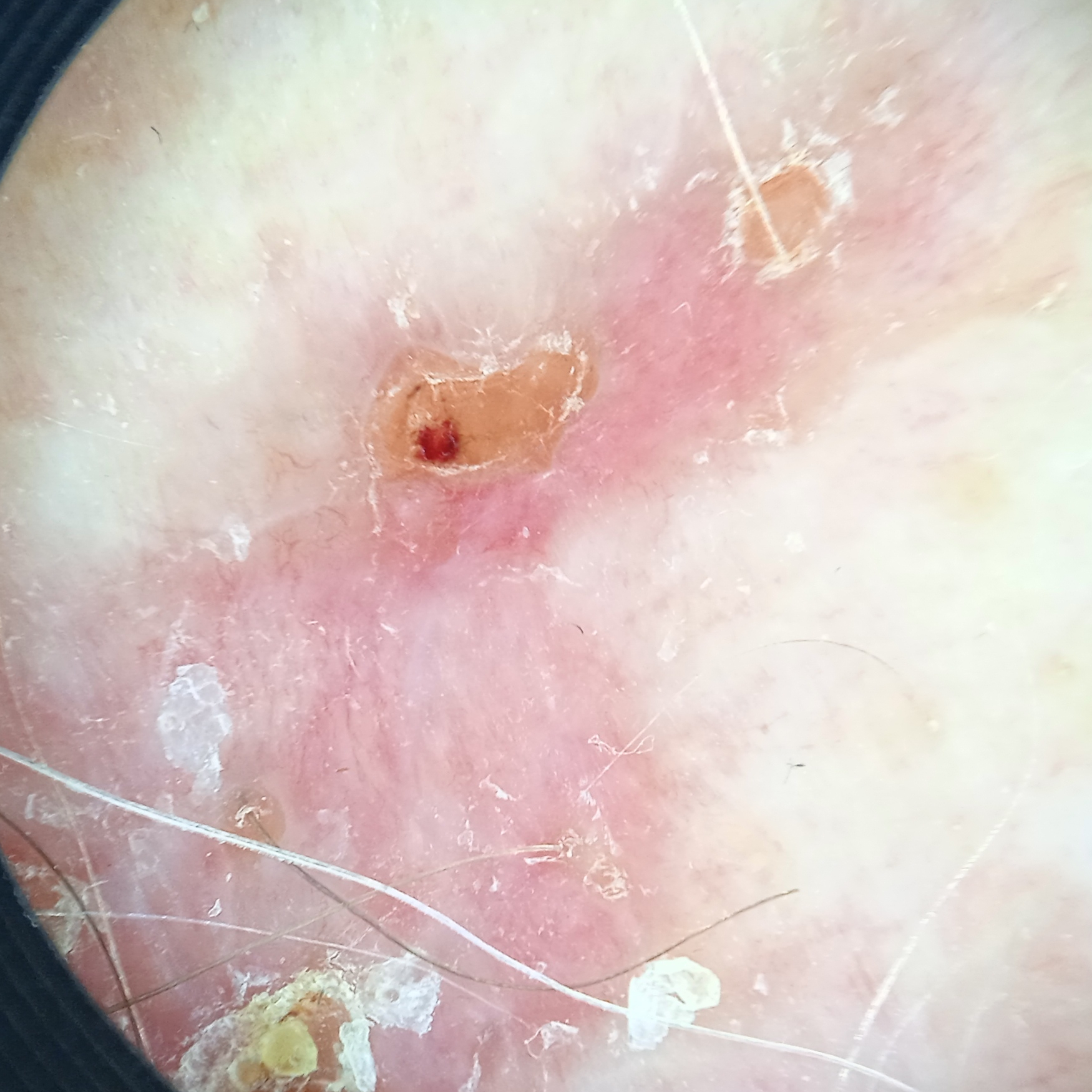image type = dermatoscopic image
referral context = clinical suspicion of basal cell carcinoma
subject = male, 67 years old
site = the torso
size = 19 mm
pathology = basal cell carcinoma (biopsy-proven)